A subject aged 47; a clinical photograph showing a skin lesion — 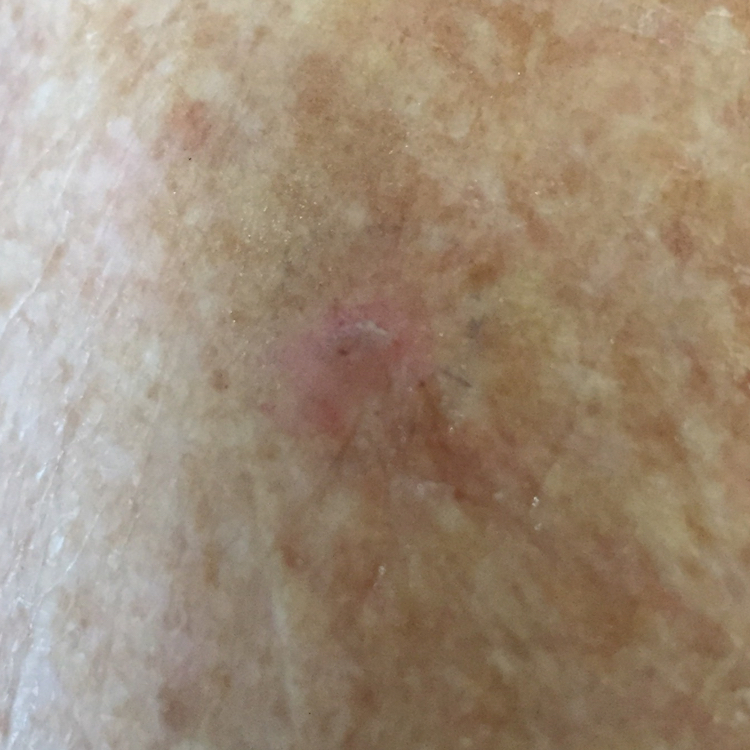<case>
<lesion_location>the face</lesion_location>
<symptoms>
<present>itching</present>
</symptoms>
<diagnosis>
<name>actinic keratosis</name>
<code>ACK</code>
<malignancy>indeterminate</malignancy>
<confirmation>clinical consensus</confirmation>
</diagnosis>
</case>